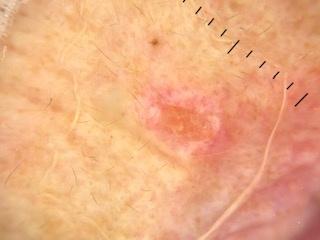A female patient in their 70s.
A skin lesion imaged with a dermatoscope.
The lesion was found on the head or neck.
Biopsy-confirmed as a basal cell carcinoma.